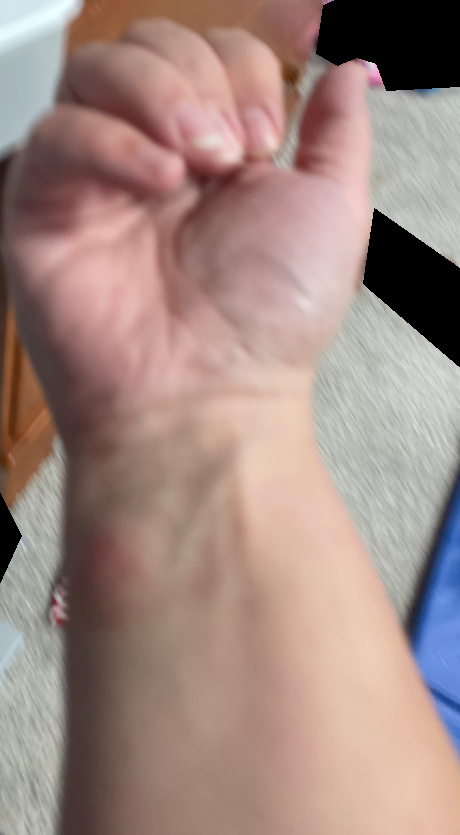Q: Could the case be diagnosed?
A: not assessable
Q: What is the framing?
A: at a distance